A female patient 26 years of age. On a questionnaire the patient reported a history of sunbed use. The patient says their skin reddens with sun exposure:
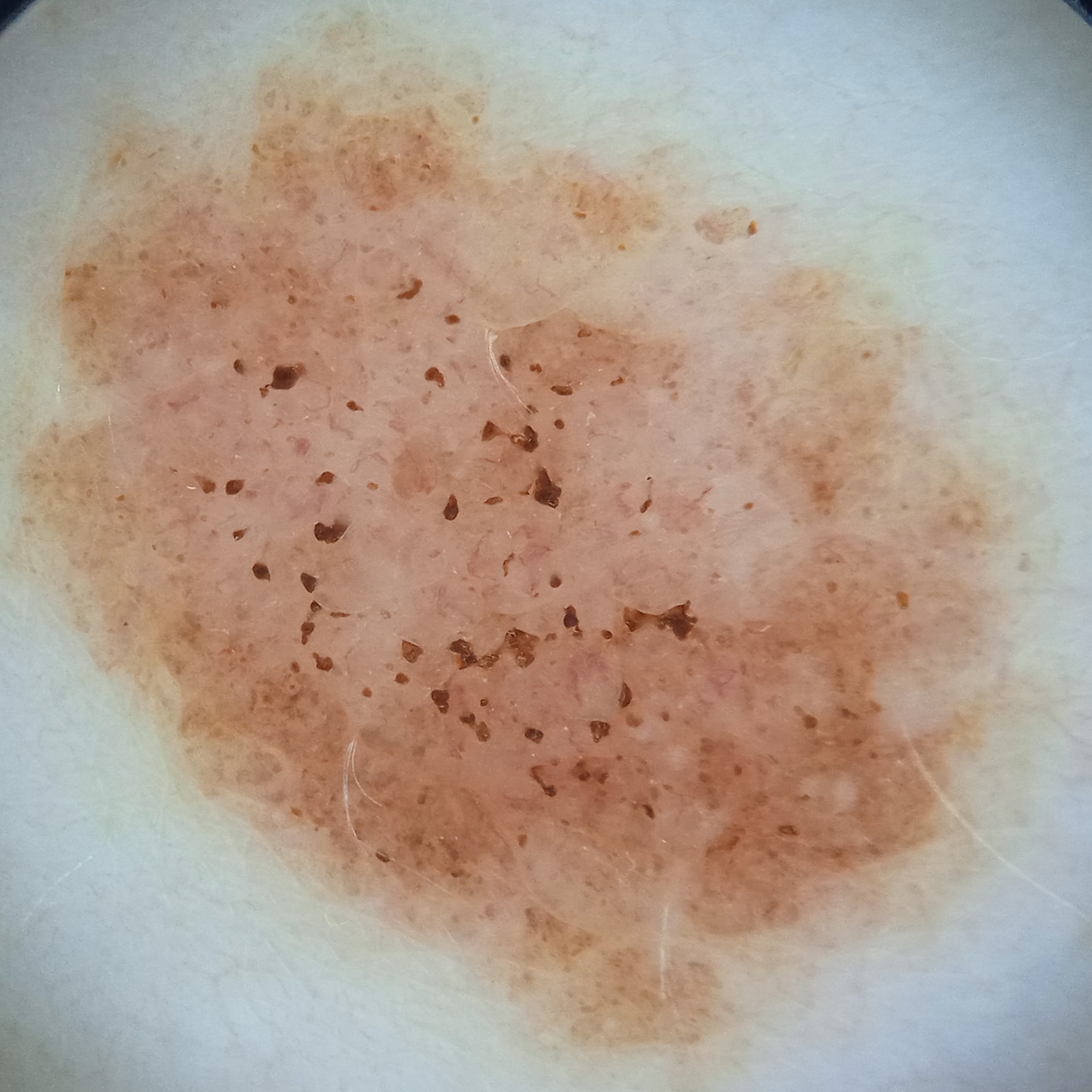Q: Where is the lesion?
A: the torso
Q: What was the diagnosis?
A: melanocytic nevus (dermatologist consensus)